A contact-polarized dermoscopy image of a skin lesion:
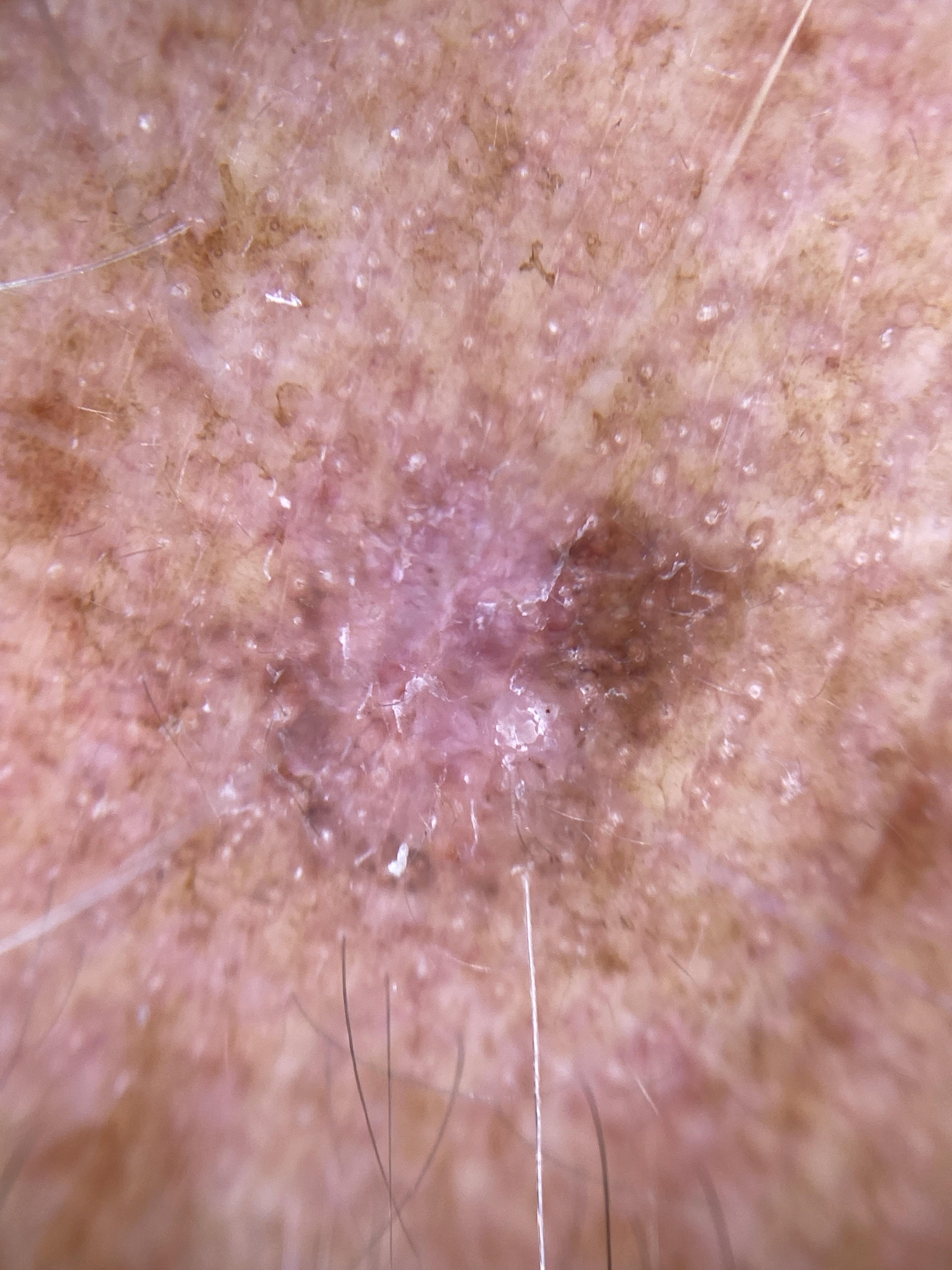| feature | finding |
|---|---|
| body site | the head or neck |
| pathology | Basal cell carcinoma (biopsy-proven) |